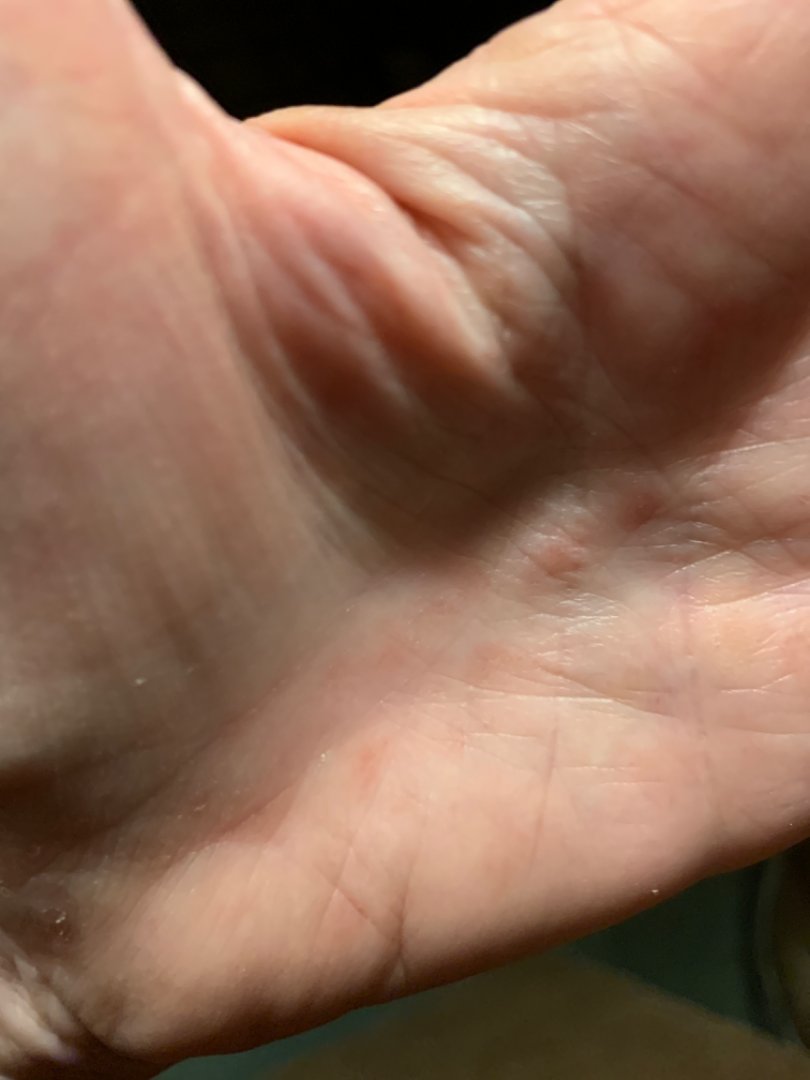Findings:
– affected area — palm
– described texture — flat
– image framing — at an angle
– differential — the impression was split between Eczema, Syphilis and Hand foot and mouth disease